The contributor is 40–49, female · located on the front of the torso · a close-up photograph:
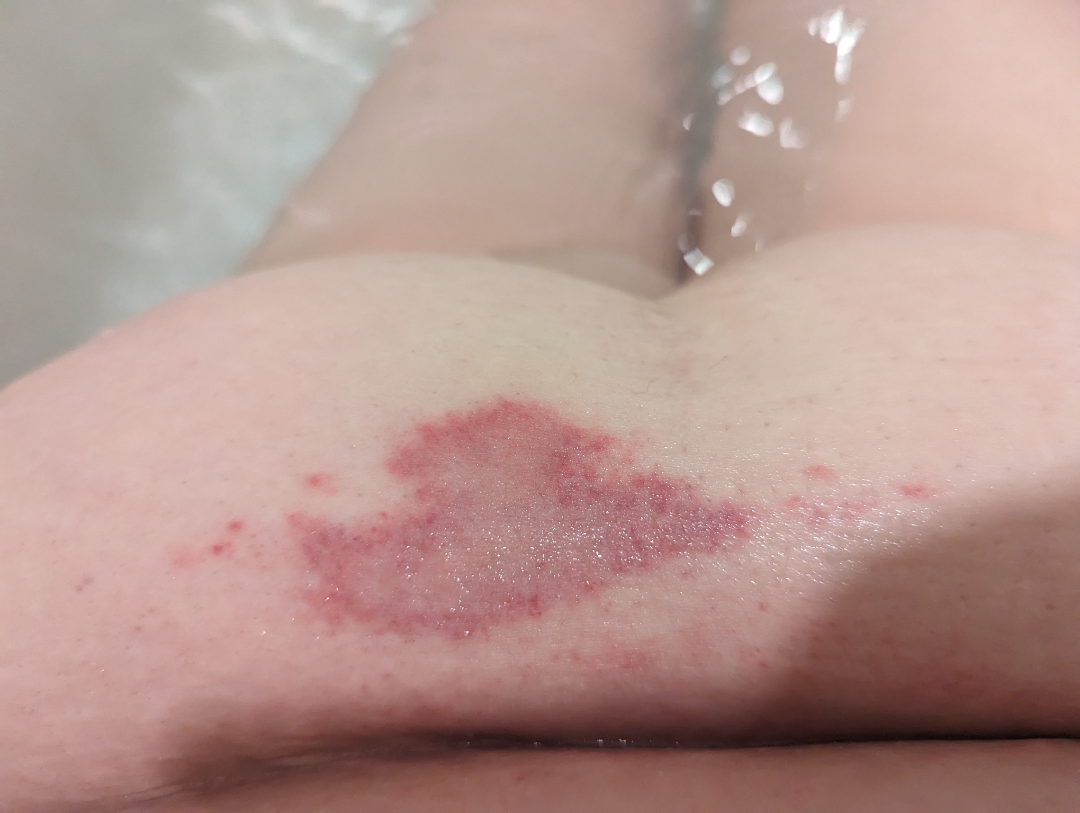Self-categorized by the patient as a rash.
The patient indicates the lesion is rough or flaky and raised or bumpy.
The patient indicates bothersome appearance.
The patient reported no systemic symptoms.
One reviewing dermatologist: most consistent with Purpura; also consider Morphea/Scleroderma.